This is a dermoscopic photograph of a skin lesion — 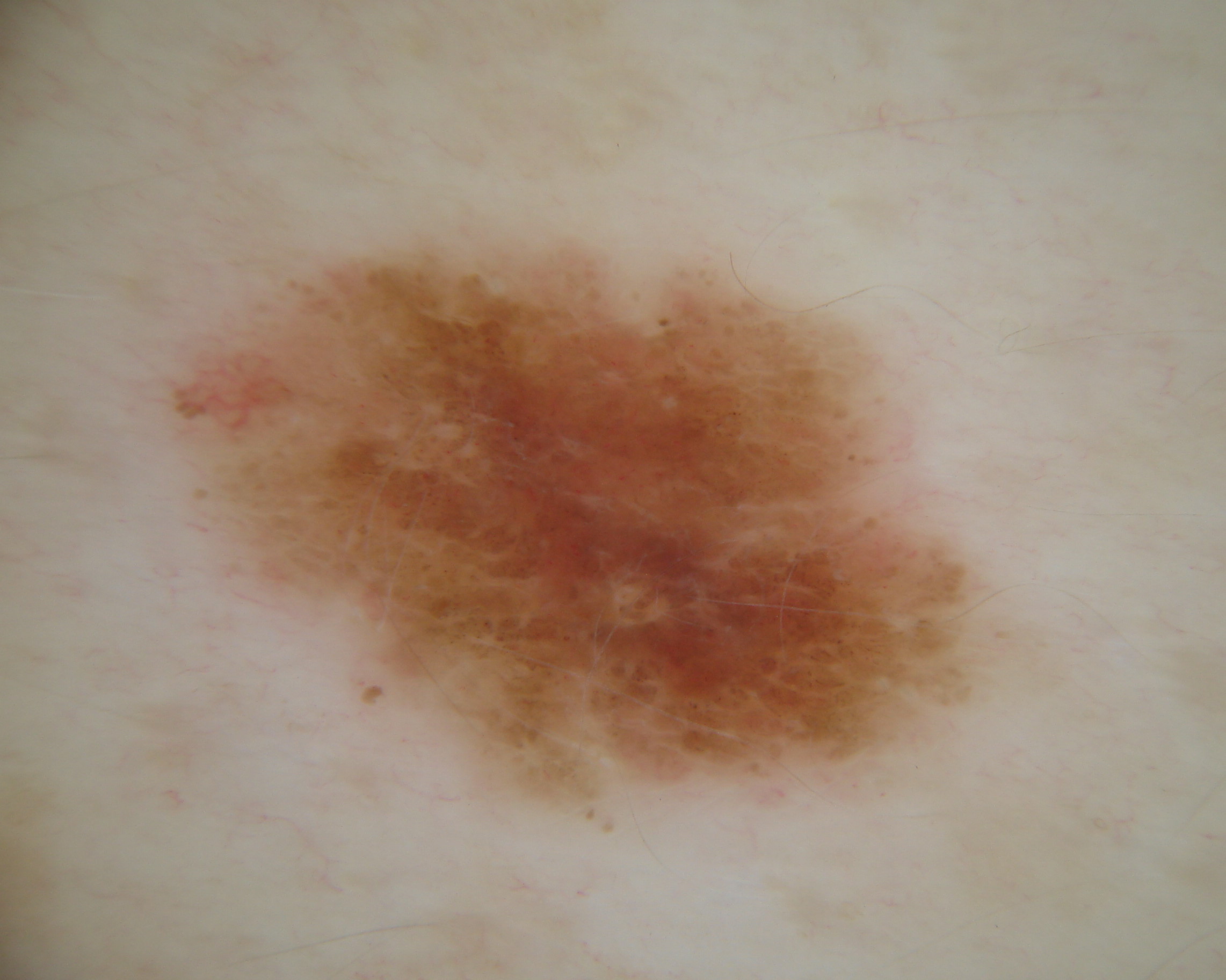Image and clinical context:
Dermoscopic examination shows negative network and globules, with no streaks, pigment network, or milia-like cysts. In (x1, y1, x2, y2) order, the lesion is located at bbox(140, 227, 988, 818).
Assessment:
Clinically diagnosed as a melanocytic nevus.